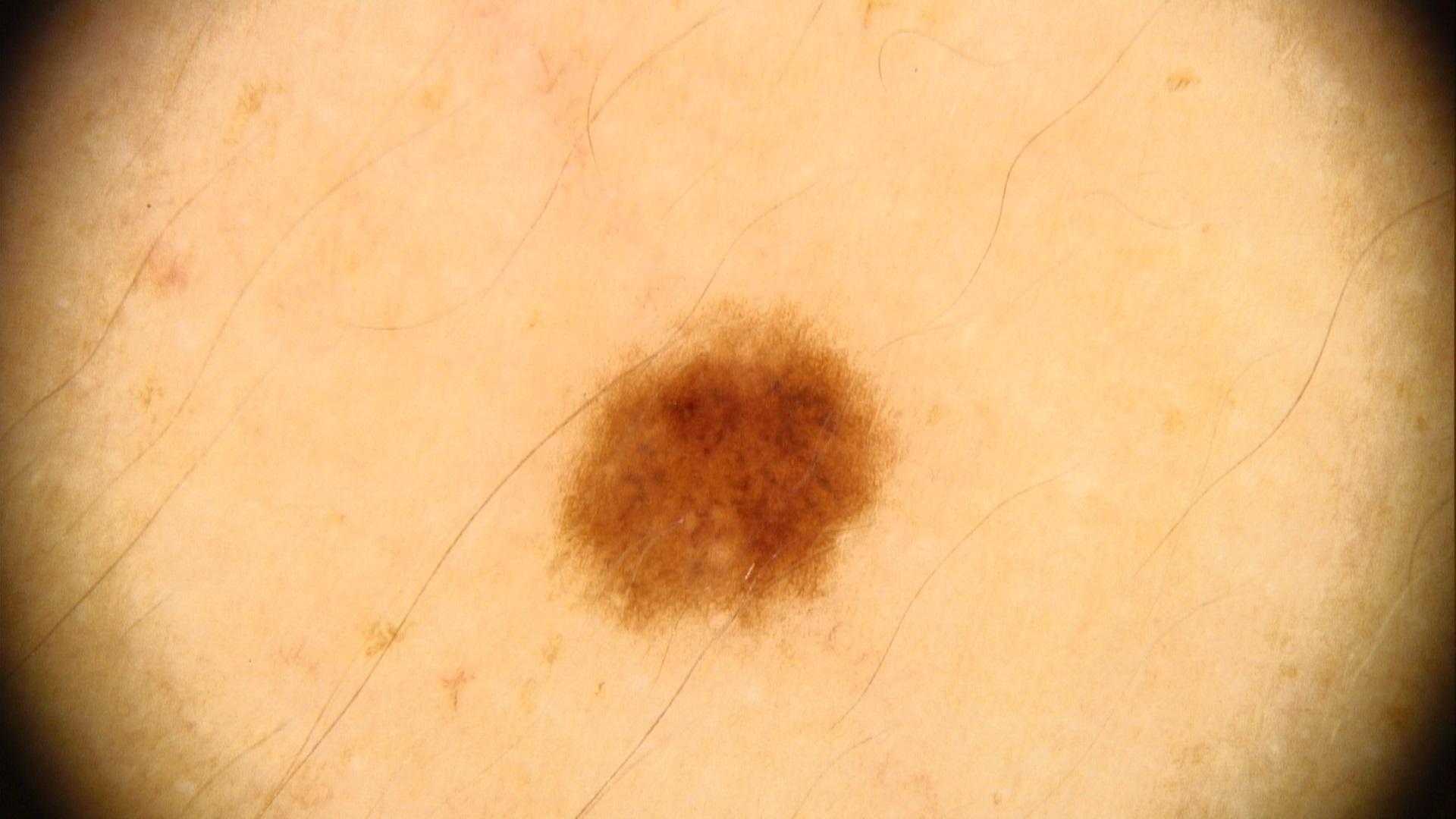Summary:
A skin lesion imaged with contact-polarized dermoscopy. Recorded as skin type III. A female subject about 30 years old. The lesion involves an upper extremity.
Assessment:
Consistent with a benign, melanocytic lesion — a nevus.